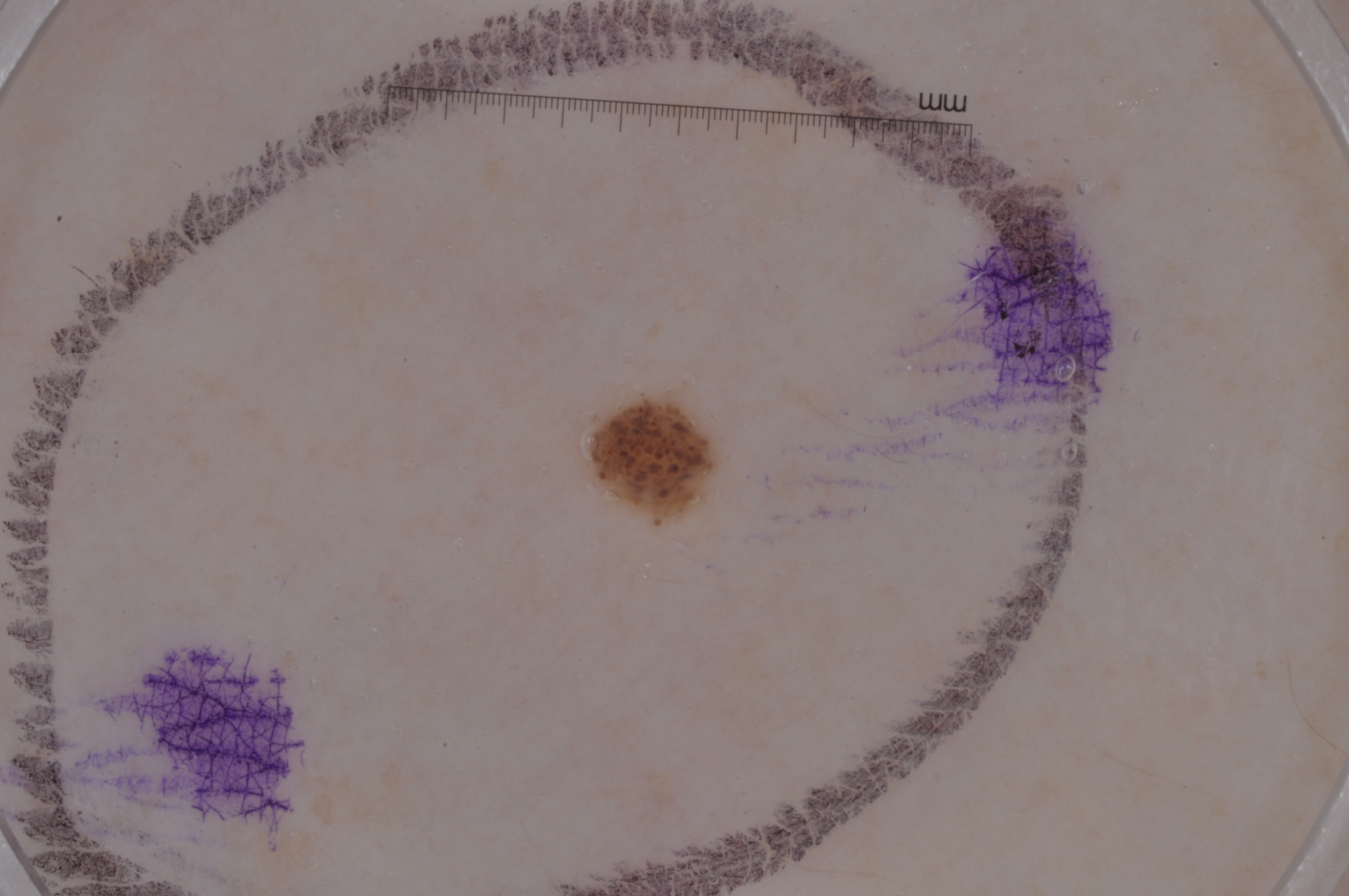| field | value |
|---|---|
| modality | dermatoscopic image of a skin lesion |
| patient | female, about 35 years old |
| lesion location | <bbox>590, 399, 716, 511</bbox> |
| lesion extent | small |
| dermoscopic features not present | streaks, pigment network, milia-like cysts, and negative network |
| impression | a melanocytic nevus |